A dermoscopic close-up of a skin lesion · the chart records a prior melanoma · the patient is FST II · a female patient in their 70s:
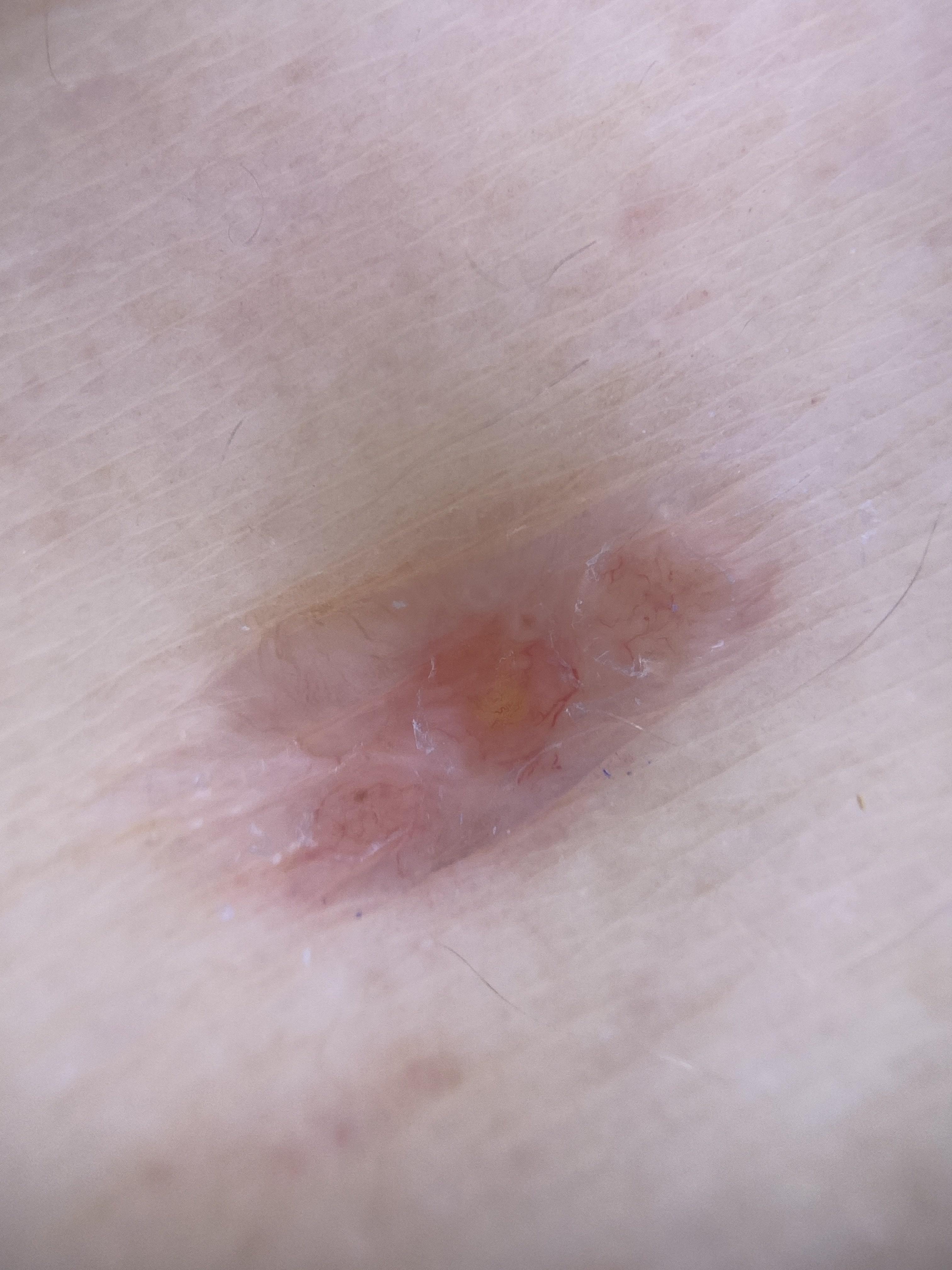Notes:
• site: the trunk
• pathology: Basal cell carcinoma (biopsy-proven)